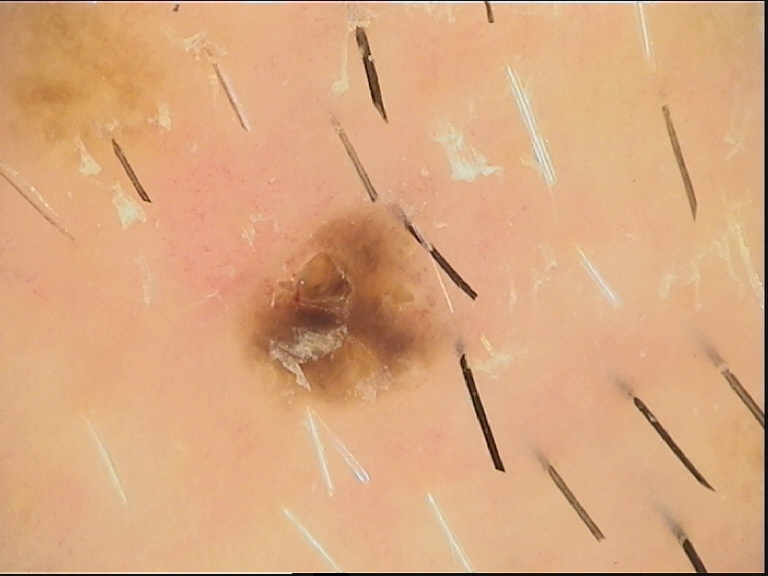diagnostic label — seborrheic keratosis (expert consensus).